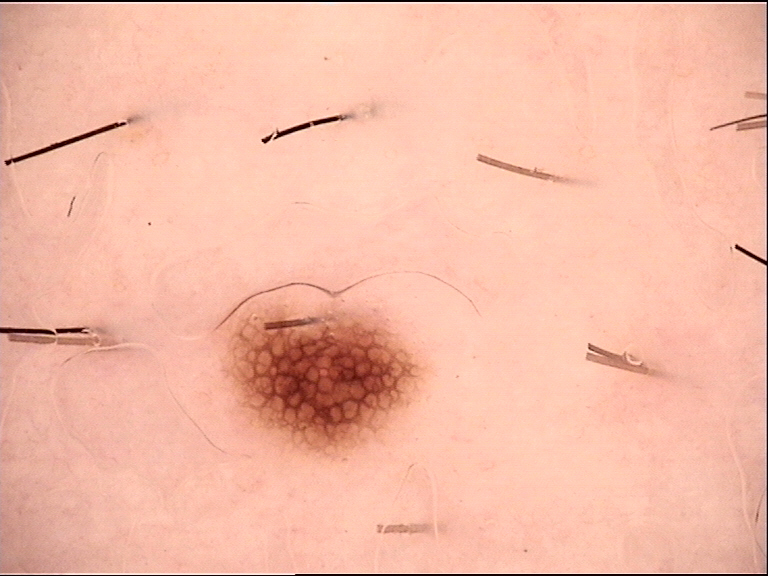Q: What is this lesion?
A: dysplastic junctional nevus (expert consensus)